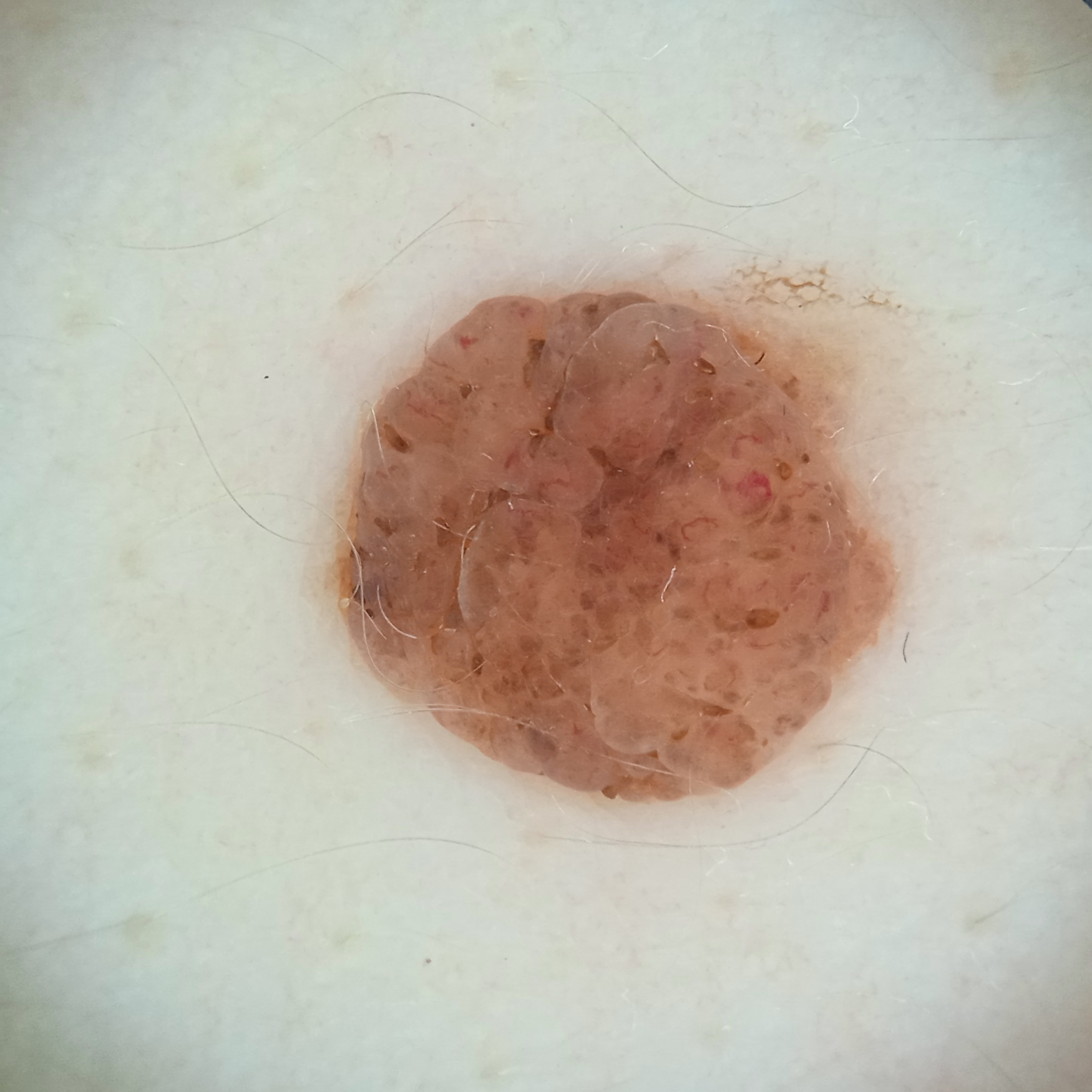Q: What was the diagnosis?
A: melanocytic nevus (dermatologist consensus)